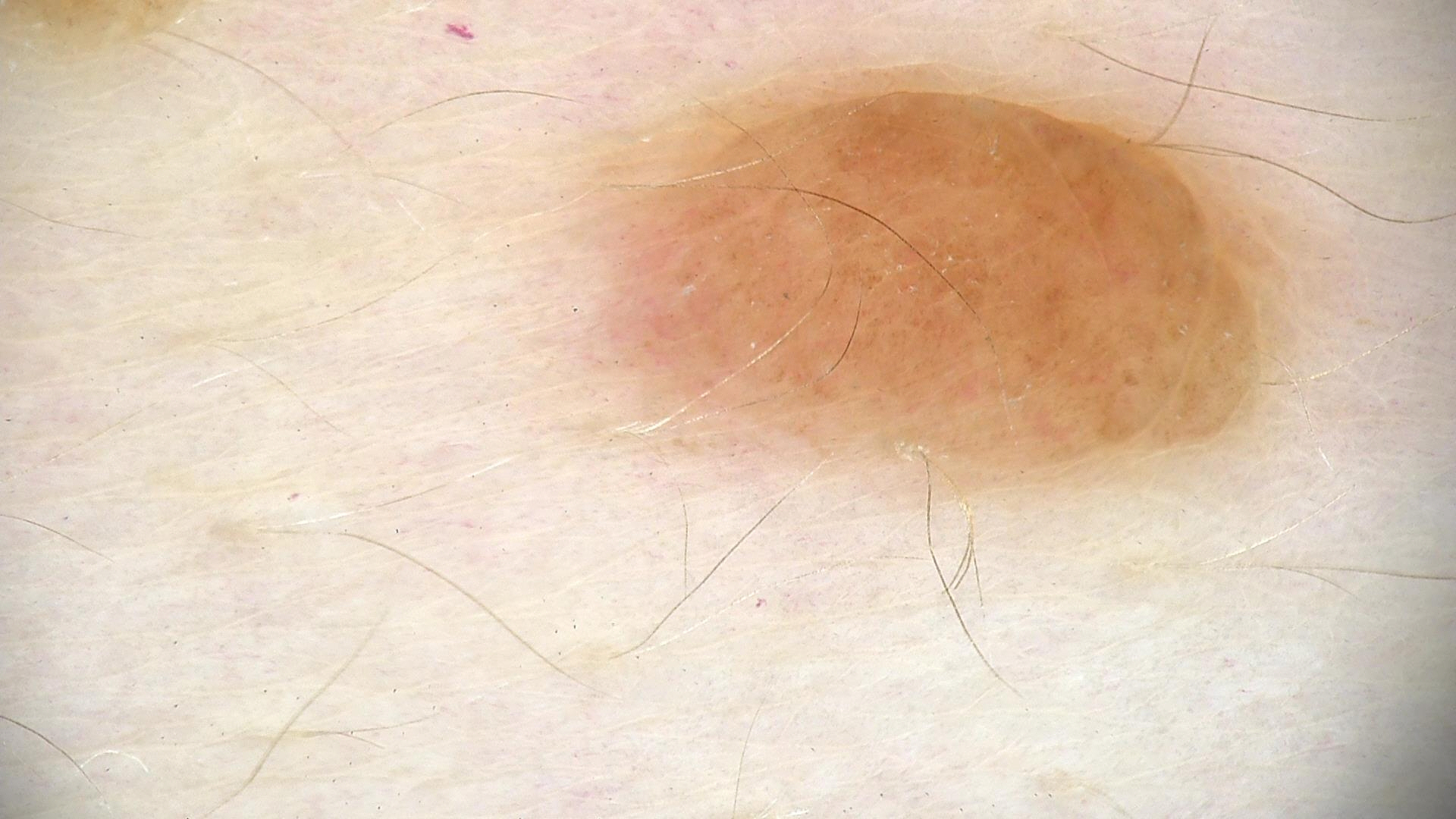Labeled as a banal lesion — a compound nevus.